A dermatoscopic image of a skin lesion: 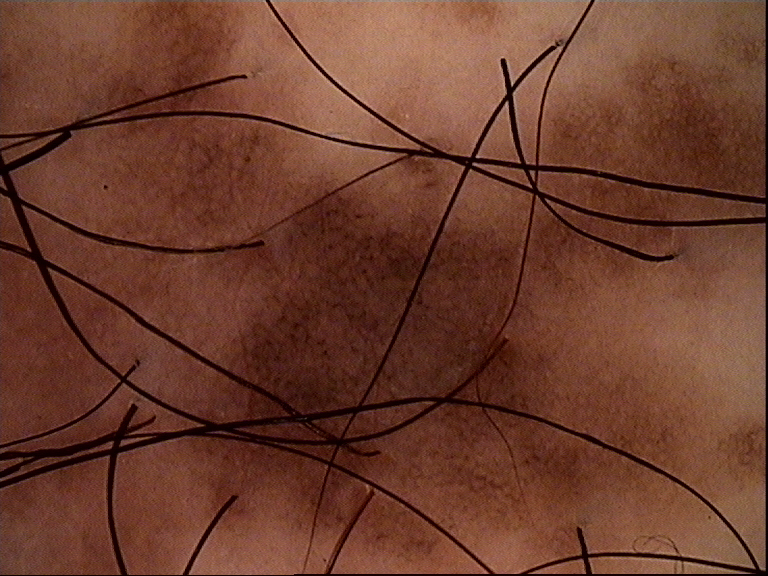Impression: Diagnosed as a banal lesion — a congenital compound nevus.